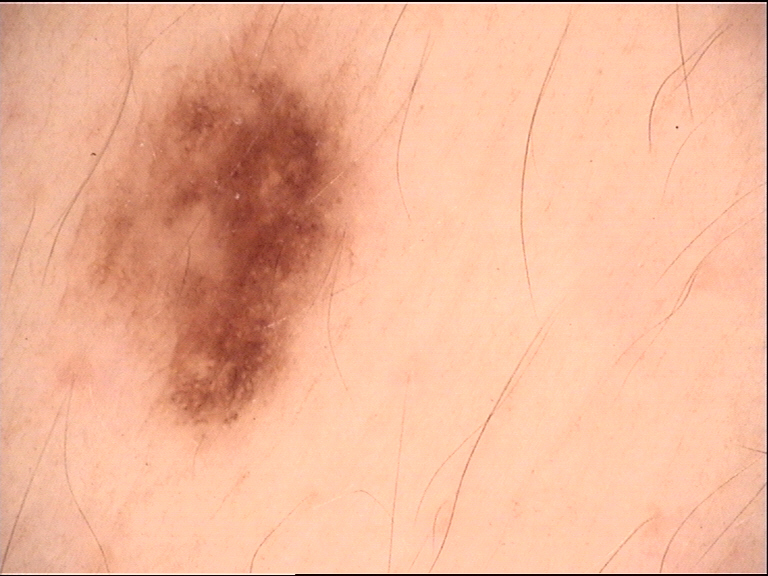Impression:
The diagnostic label was a dysplastic junctional nevus.